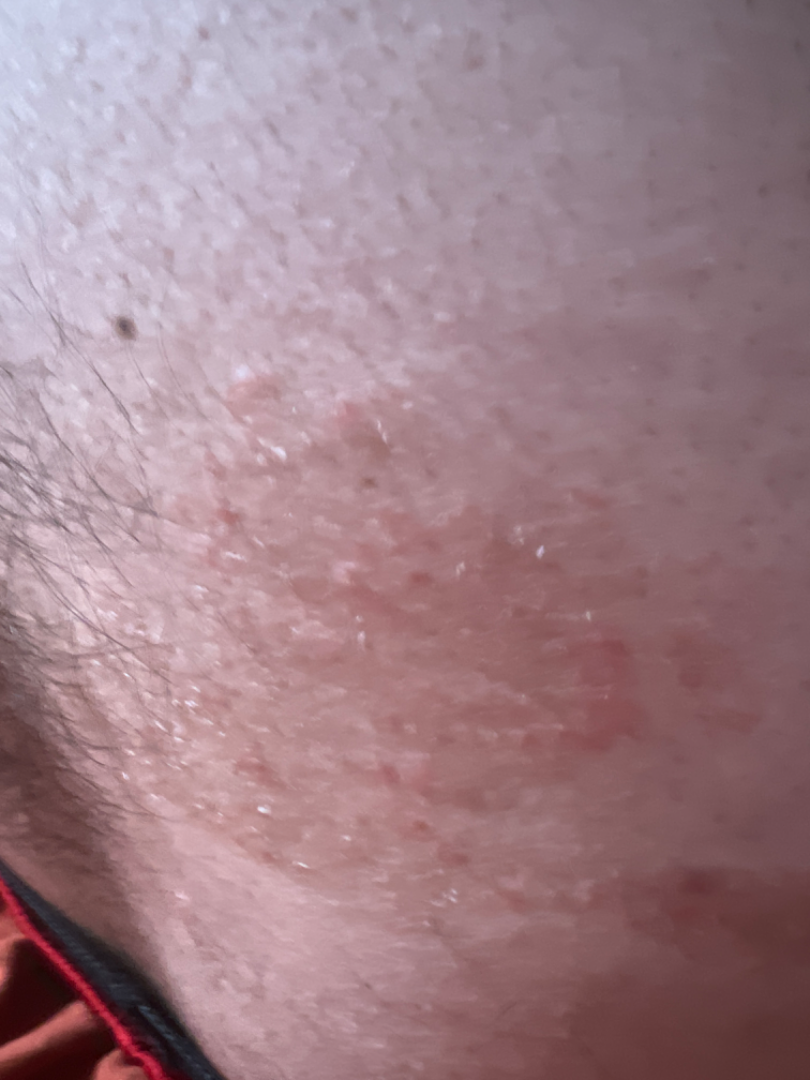<summary>
  <differential>
    <leading>Tinea</leading>
    <considered>Psoriasis, Eczema</considered>
  </differential>
</summary>